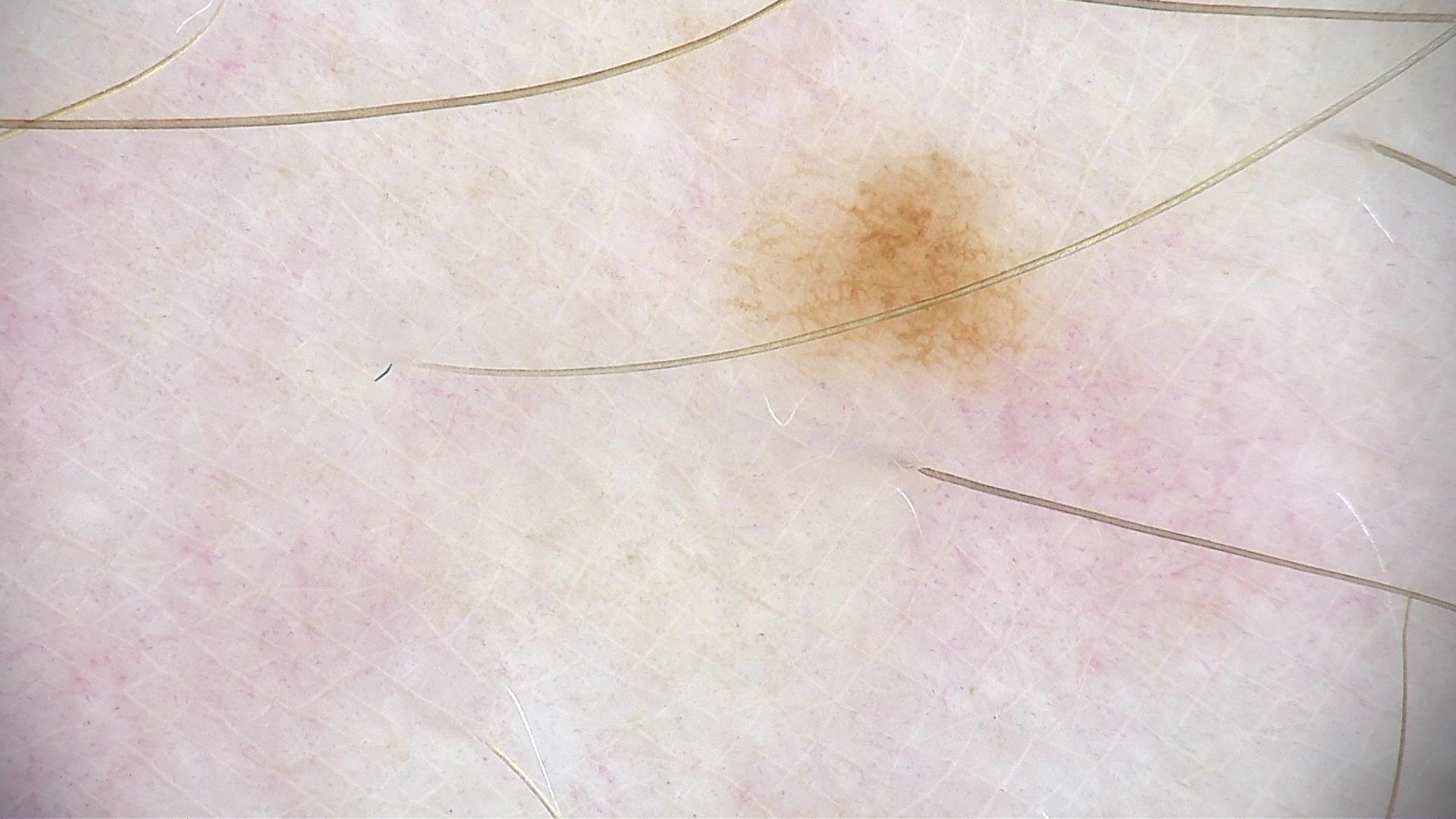Impression: Diagnosed as a dysplastic junctional nevus.